A skin lesion imaged with a dermatoscope:
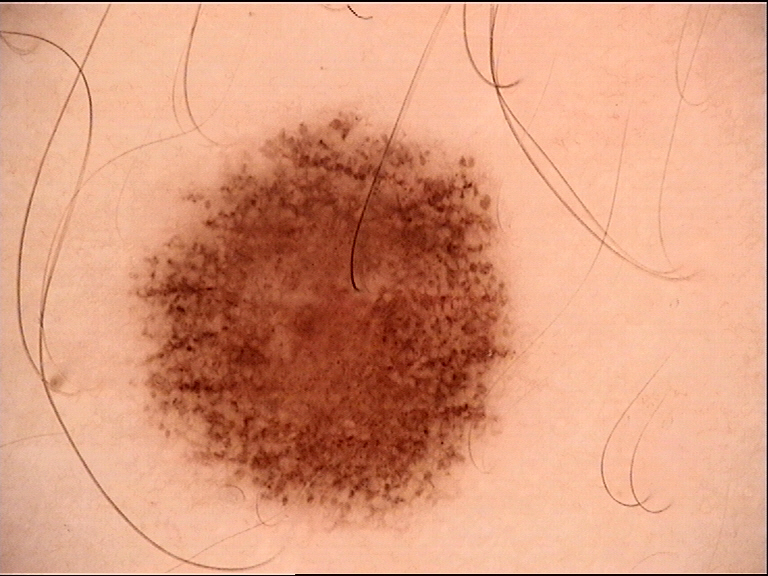category — banal; assessment — junctional nevus (expert consensus).